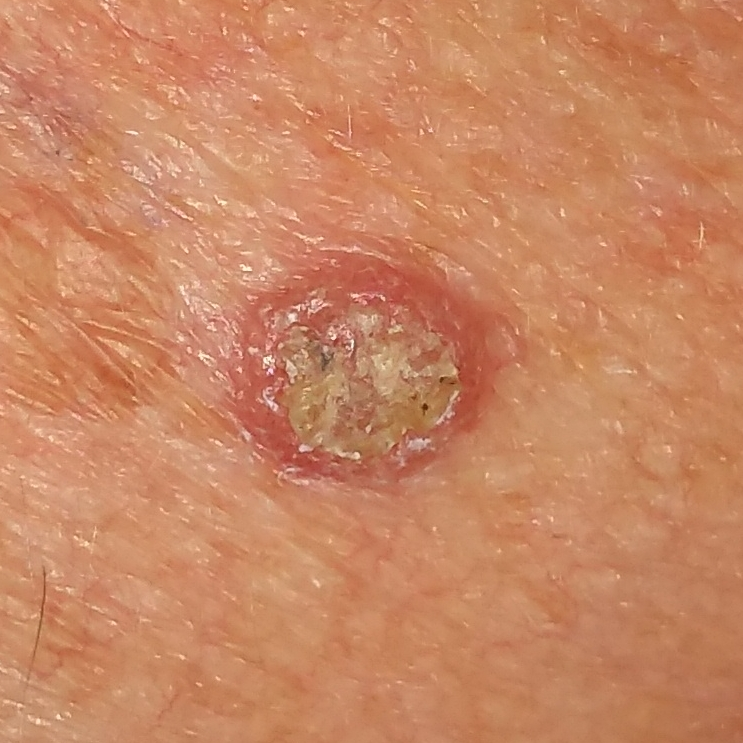  skin_type: II
  patient:
    age: 80
    gender: male
  image: clinical photo
  lesion_location: the chest
  lesion_size:
    diameter_1_mm: 3.0
    diameter_2_mm: 2.0
  symptoms:
    present:
      - elevation
      - itching
    absent:
      - bleeding
  diagnosis:
    name: seborrheic keratosis
    code: SEK
    malignancy: benign
    confirmation: histopathology